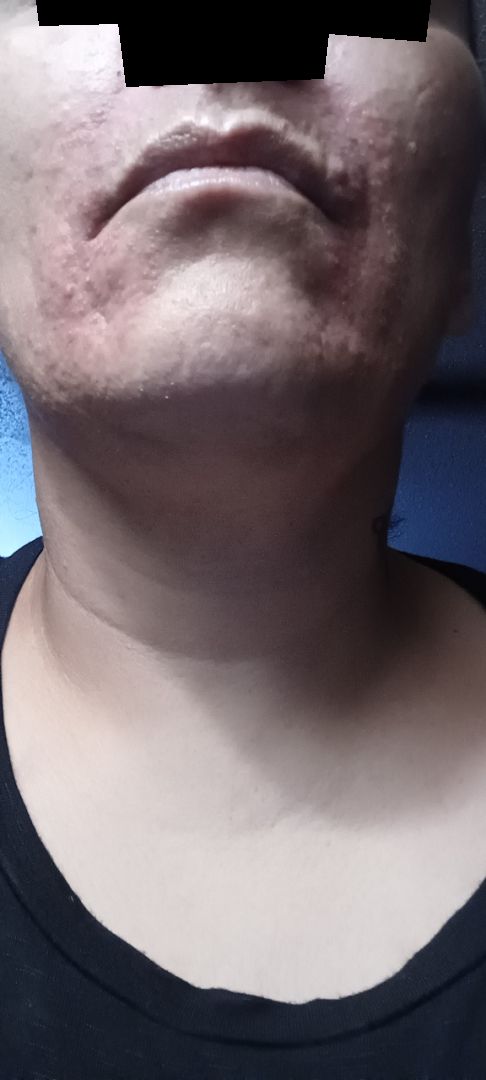Q: Could the case be diagnosed?
A: unable to determine
Q: How long has this been present?
A: three to twelve months
Q: Reported symptoms?
A: bothersome appearance, itching and burning
Q: Who is the patient?
A: female
Q: How does the lesion feel?
A: raised or bumpy and rough or flaky
Q: Any systemic symptoms?
A: joint pain
Q: How was the photo taken?
A: close-up